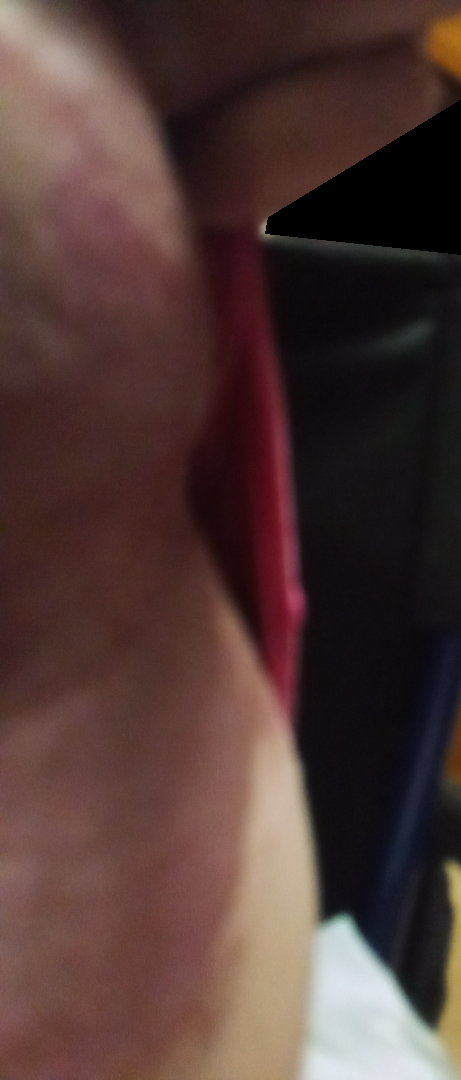Most likely Psoriasis; also on the differential is Intertrigo; possibly Candidal intertrigo.